By history, prior malignancy (patient or family). Recorded as Fitzpatrick skin type III. A male subject in their 50s.
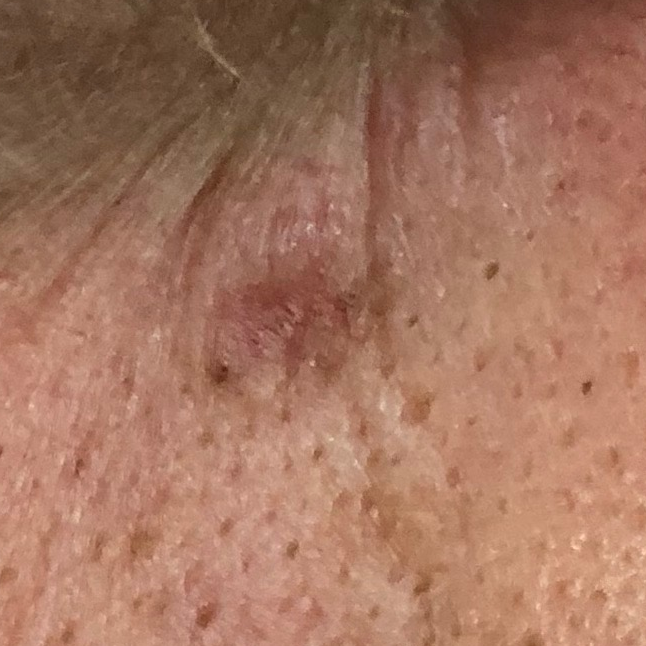The lesion involves the face. The lesion is roughly 6 by 6 mm. Histopathologically confirmed as a skin cancer — a basal cell carcinoma.